A female patient about 35 years old · dermoscopy of a skin lesion.
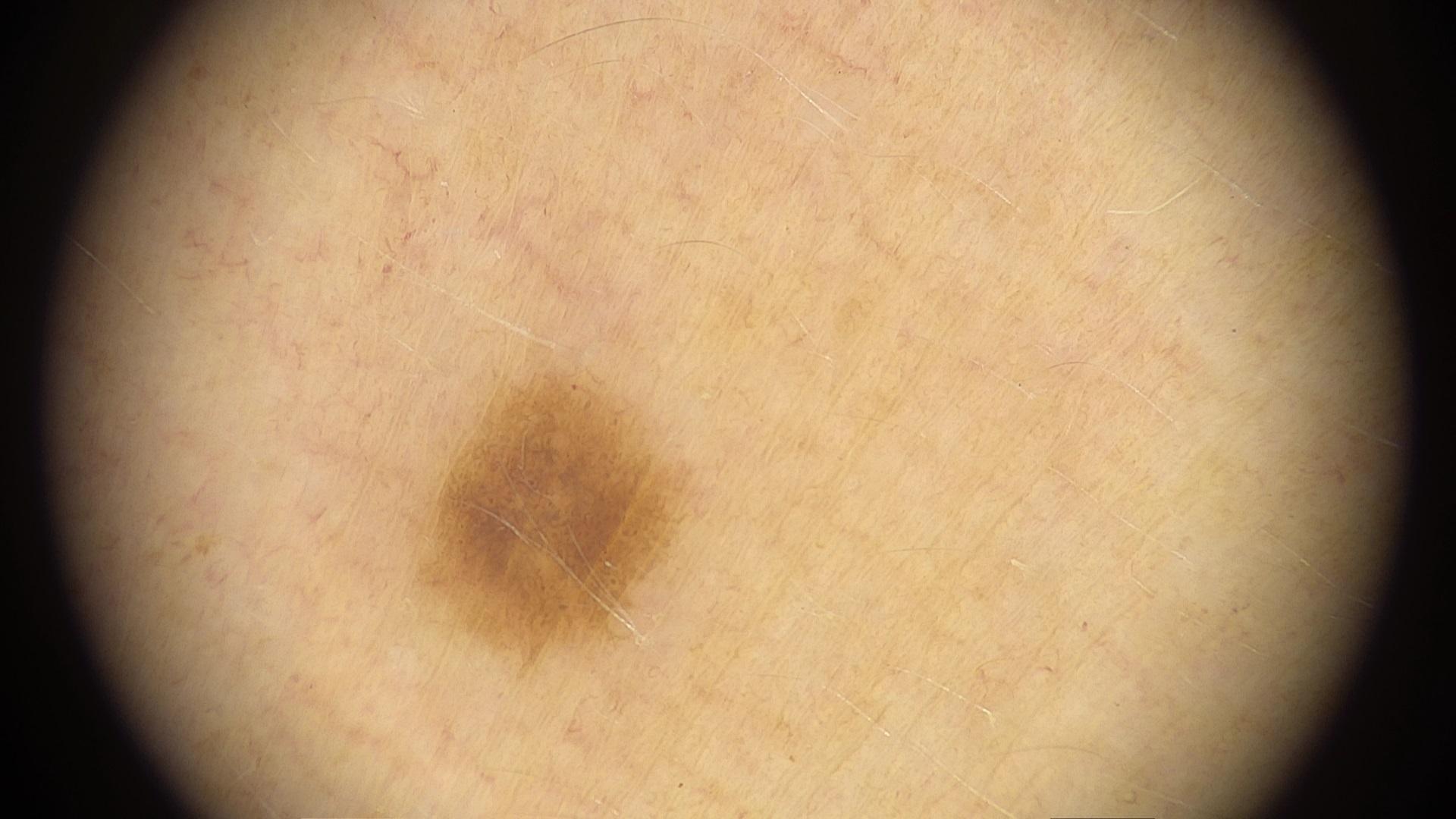Conclusion: The diagnostic impression was a nevus.